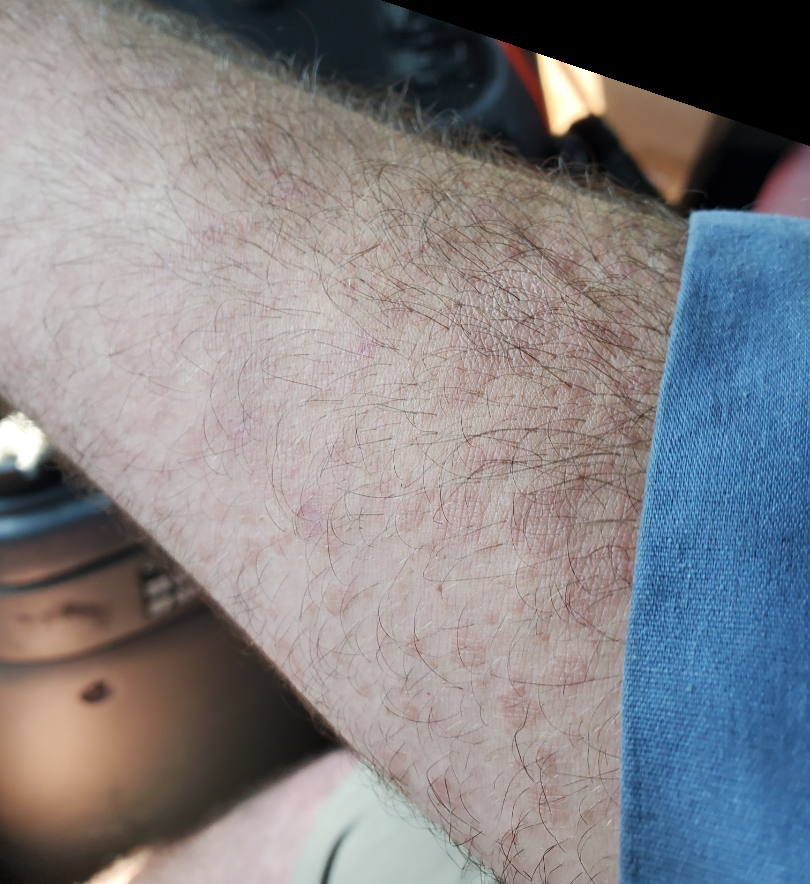  assessment: unable to determine
  shot_type: at an angle